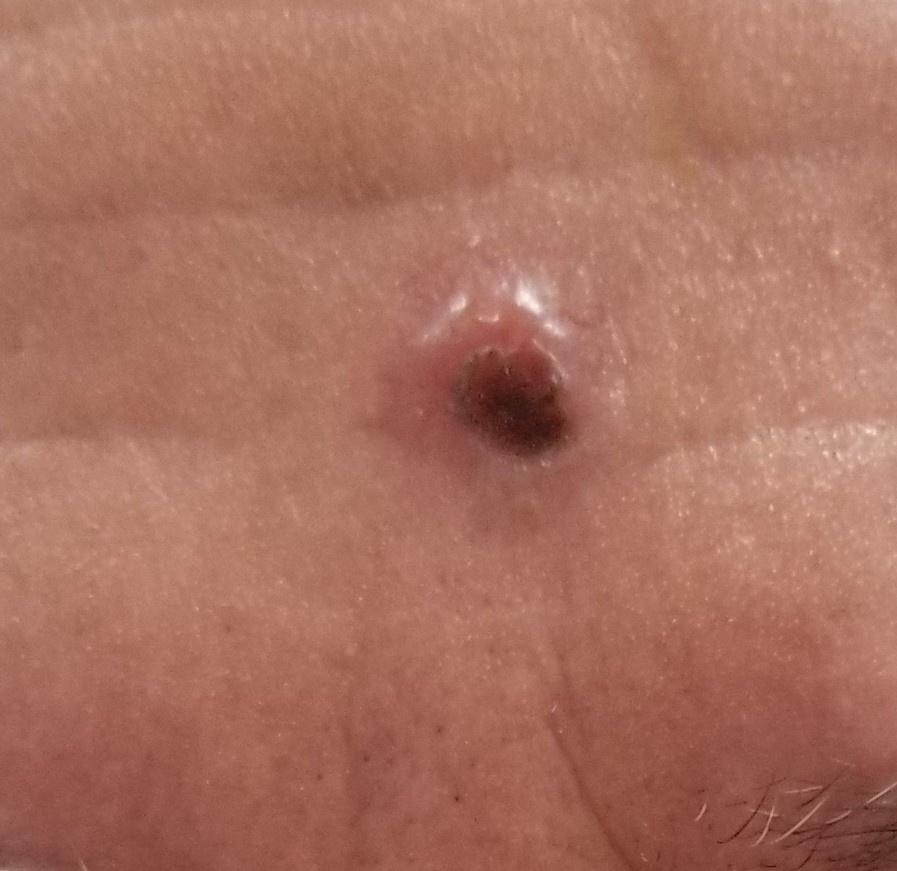Summary:
A male patient about 75 years old. A clinical overview photograph of a skin lesion. The lesion is located on the head or neck.
Conclusion:
On biopsy, the diagnosis was a basal cell carcinoma.